A dermatoscopic image of a skin lesion.
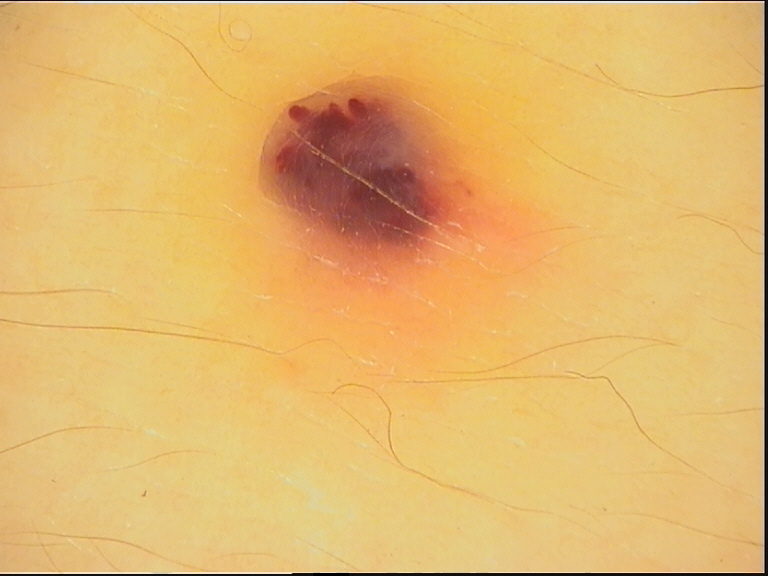label = hemangioma (expert consensus).